Male contributor, age 50–59; the photograph was taken at an angle; the affected area is the arm.
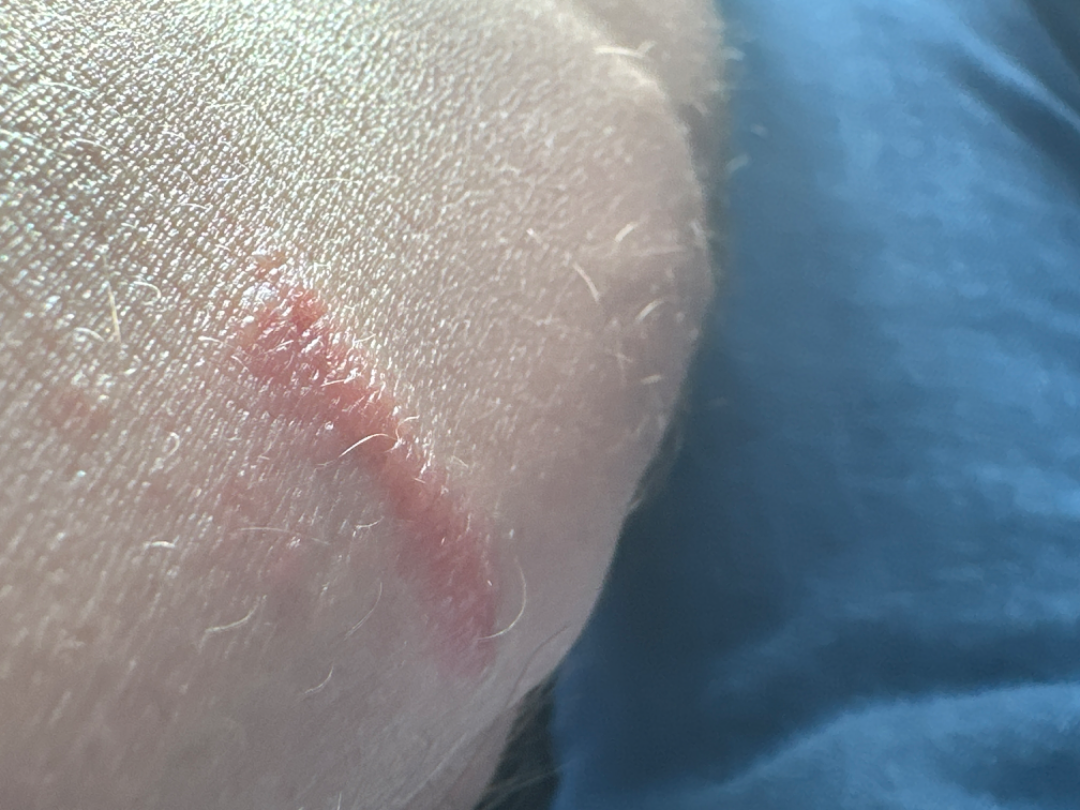Findings: The reviewing dermatologists' impression was: most likely Allergic Contact Dermatitis; also on the differential is Insect Bite.